The photograph was taken at a distance — 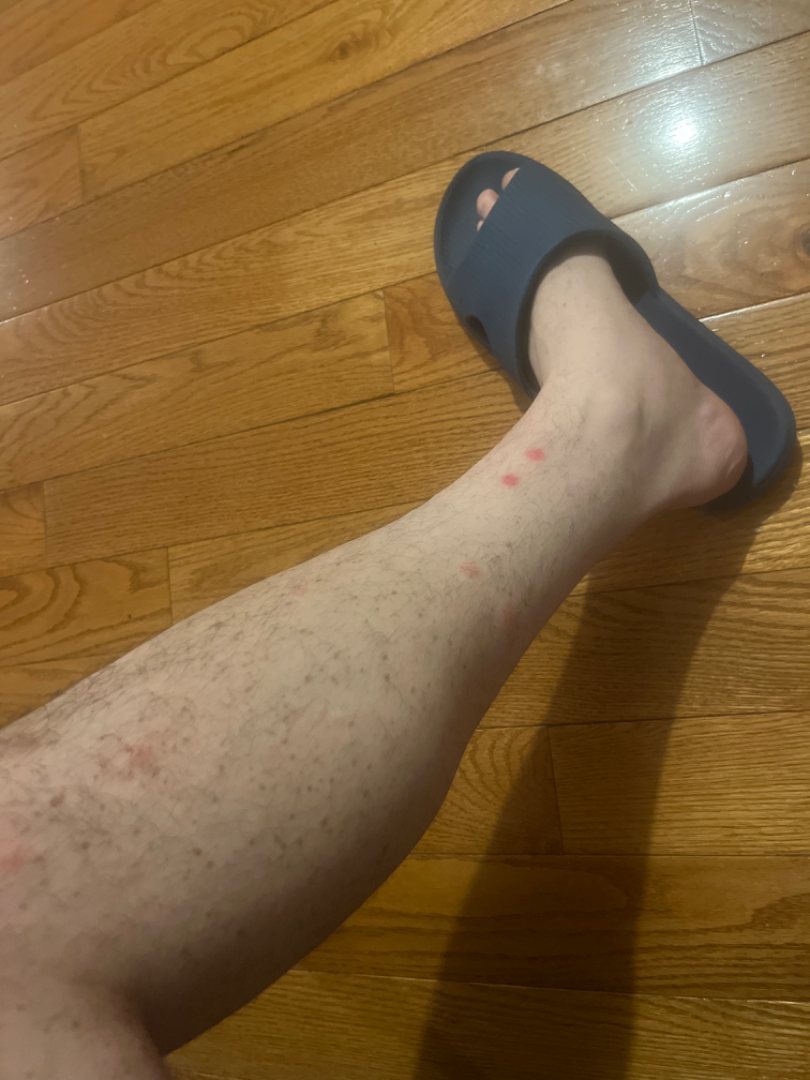Impression:
No differential diagnosis could be assigned on photographic review.